The arm is involved; this is a close-up image:
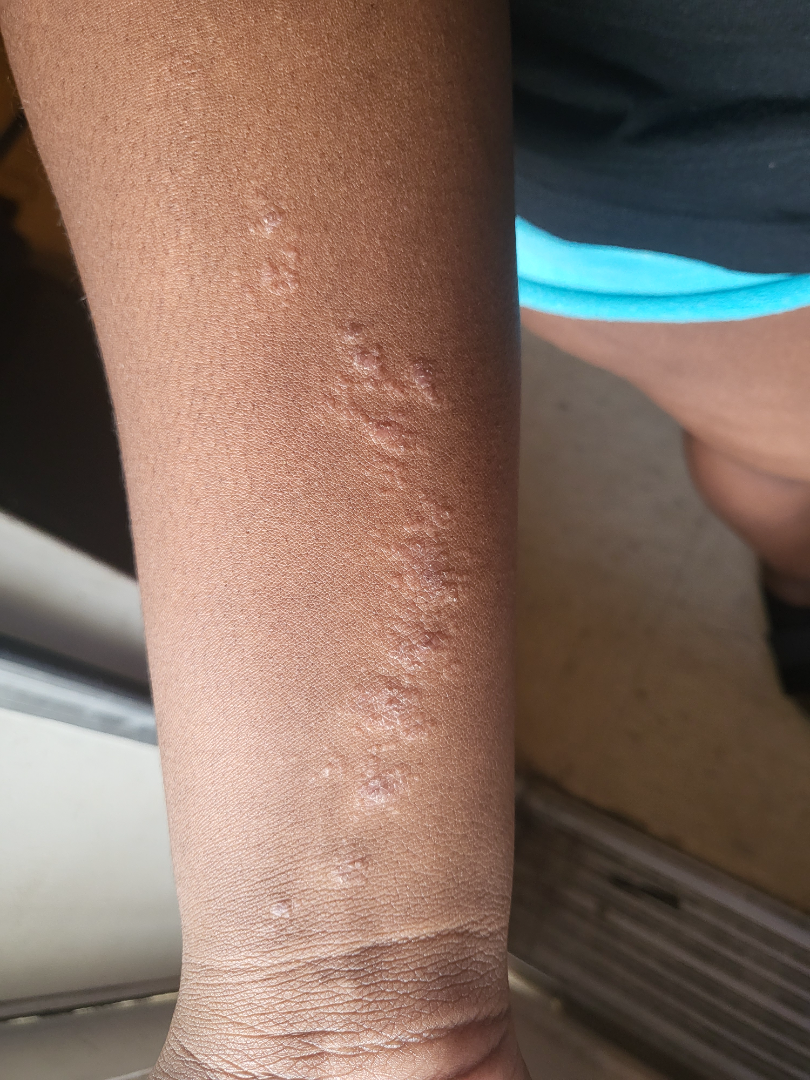Findings: Reviewed remotely by one dermatologist: the impression on review was Lichen striatus.